A dermoscopic image of a skin lesion: 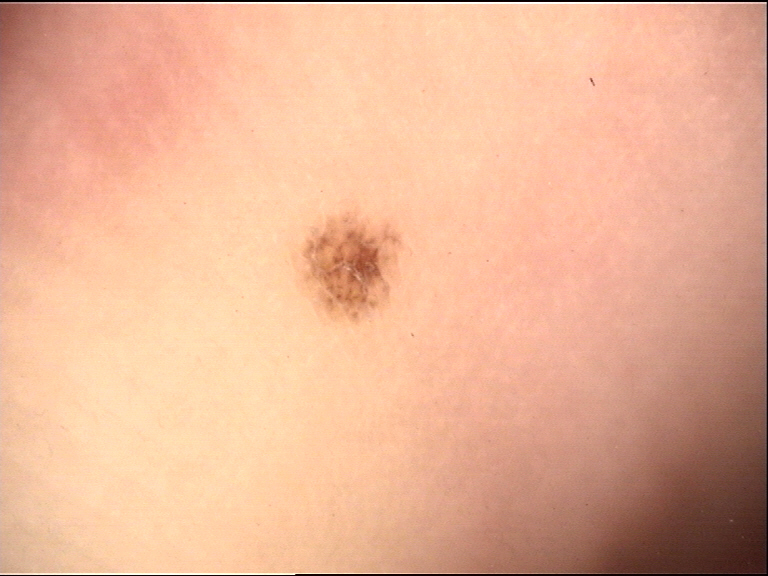diagnosis = acral dysplastic junctional nevus (expert consensus).